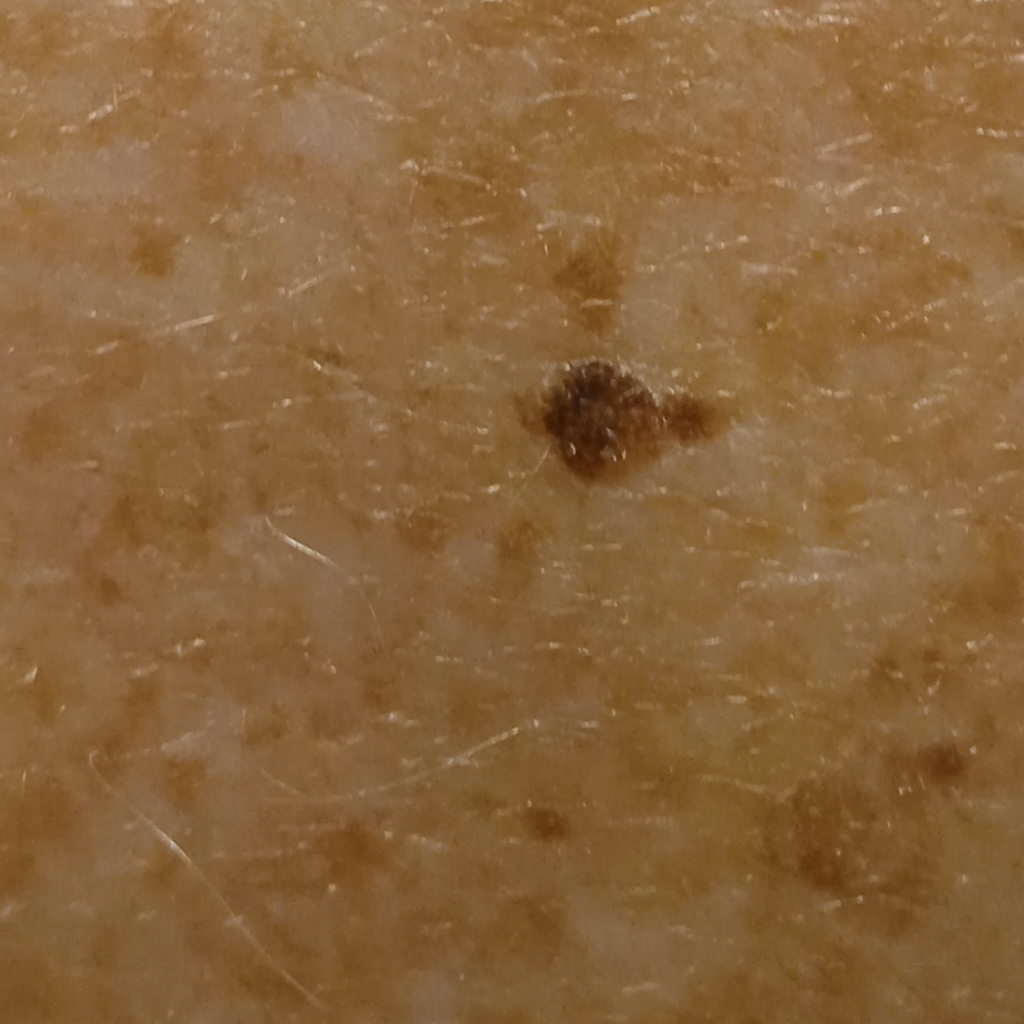{
  "referral": "research study (no referral diagnosis)",
  "image": "clinical photo",
  "mole_burden": "numerous melanocytic nevi",
  "risk_factors": {
    "positive": [
      "a personal history of cancer"
    ]
  },
  "patient": {
    "age": 73,
    "sex": "male"
  },
  "lesion_location": "the back",
  "lesion_size": {
    "diameter_mm": 5.5
  },
  "diagnosis": {
    "name": "seborrheic keratosis",
    "malignancy": "benign"
  }
}